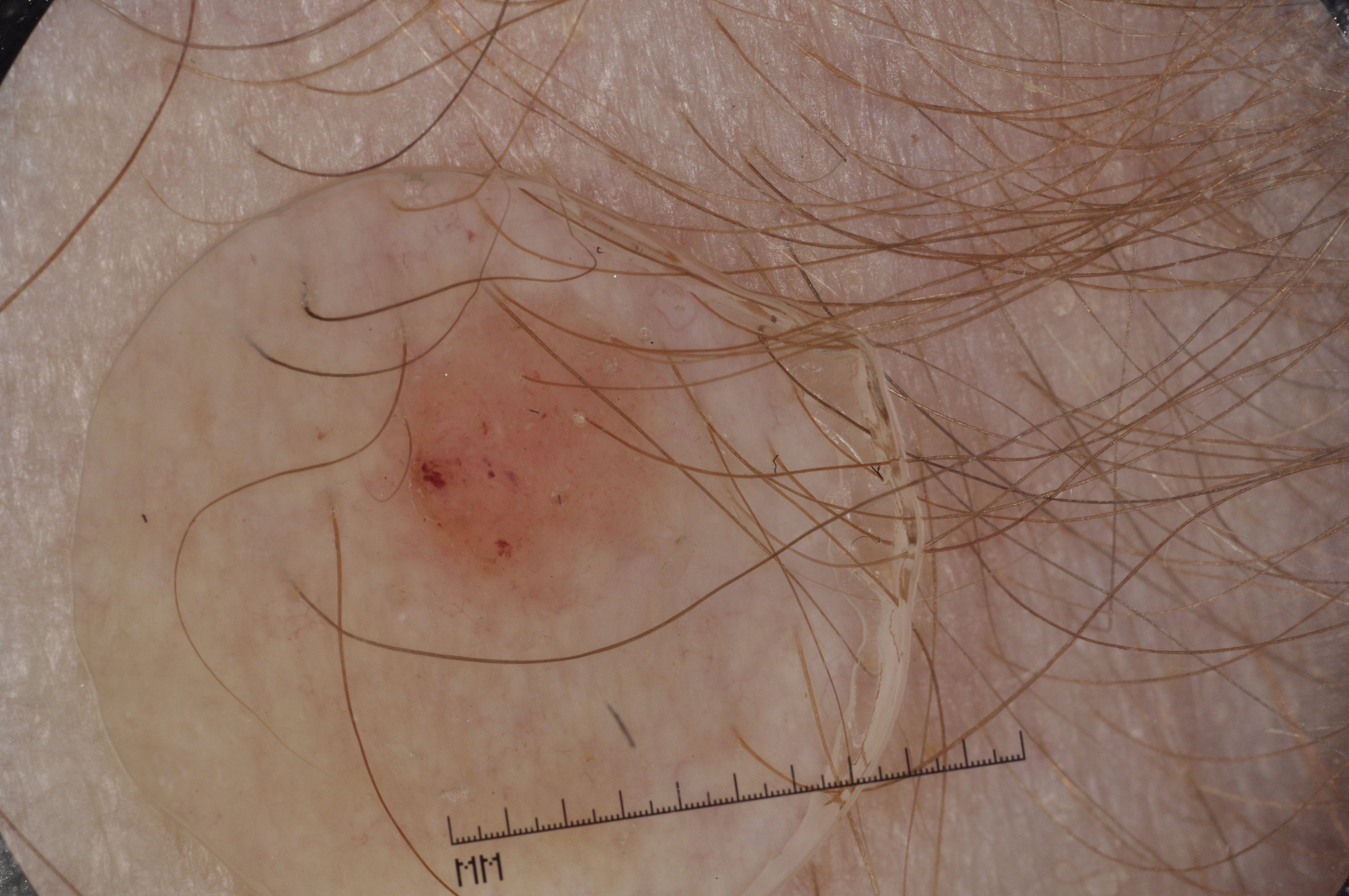Summary: A female patient, aged 68-72. A dermoscopy image of a single skin lesion. The lesion covers approximately 8% of the dermoscopic field. The visible lesion spans bbox(345, 266, 713, 637). Dermoscopically, the lesion shows no negative network, milia-like cysts, streaks, or pigment network. Impression: Diagnosed as a seborrheic keratosis, a benign skin lesion.